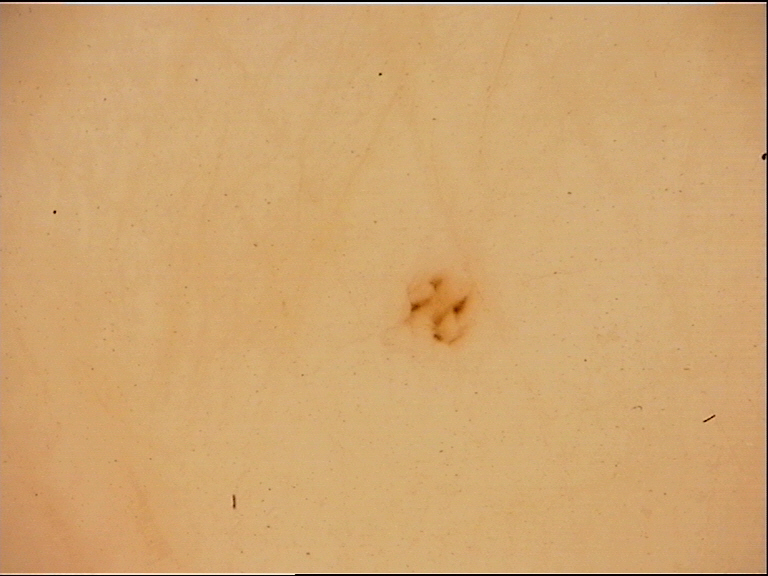A dermoscopic close-up of a skin lesion. This is a banal lesion. The diagnostic label was an acral junctional nevus.